A skin lesion imaged with a dermatoscope. A female patient about 40 years old.
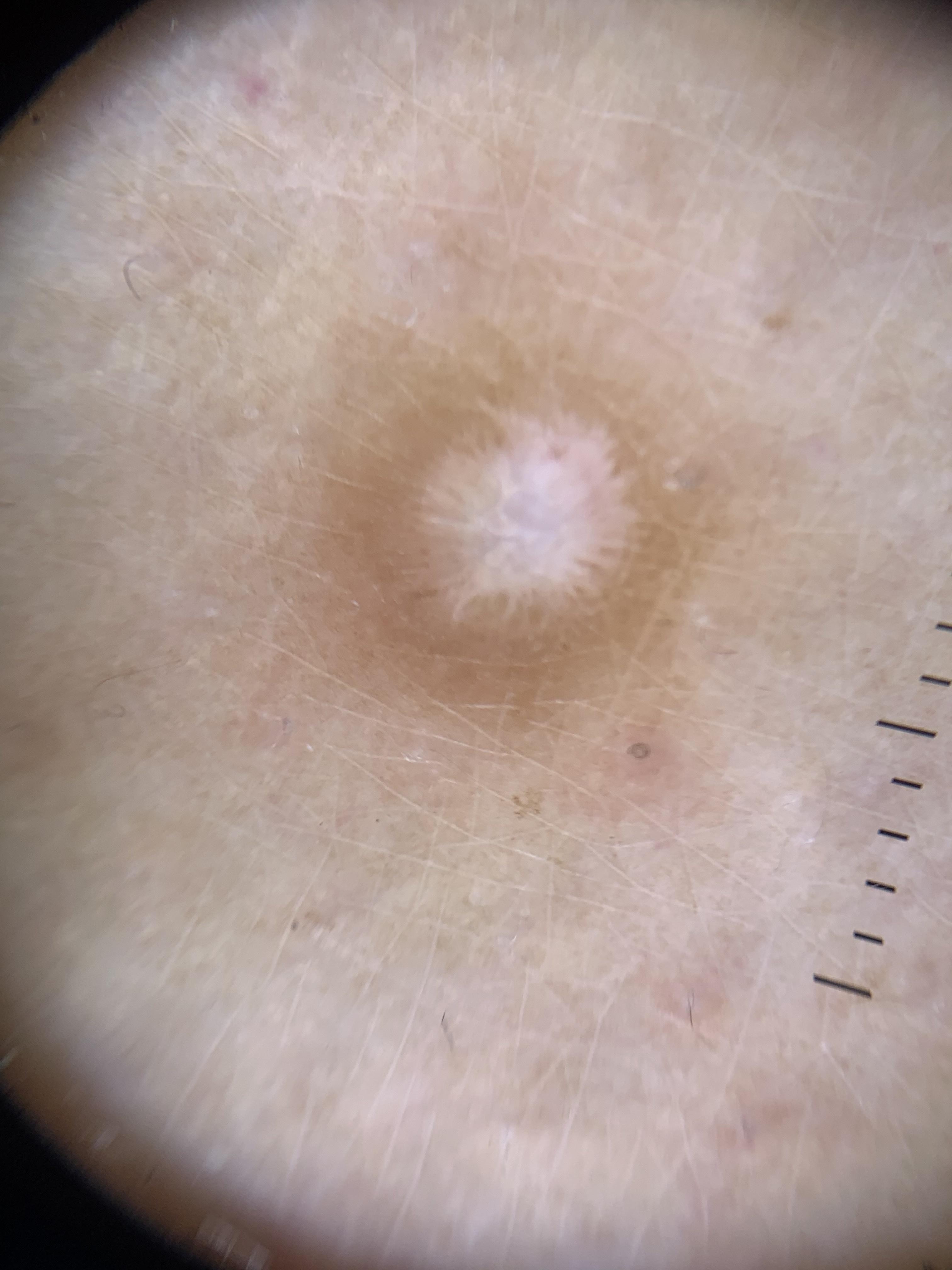site = a lower extremity | pathology = Dermatofibroma (biopsy-proven).